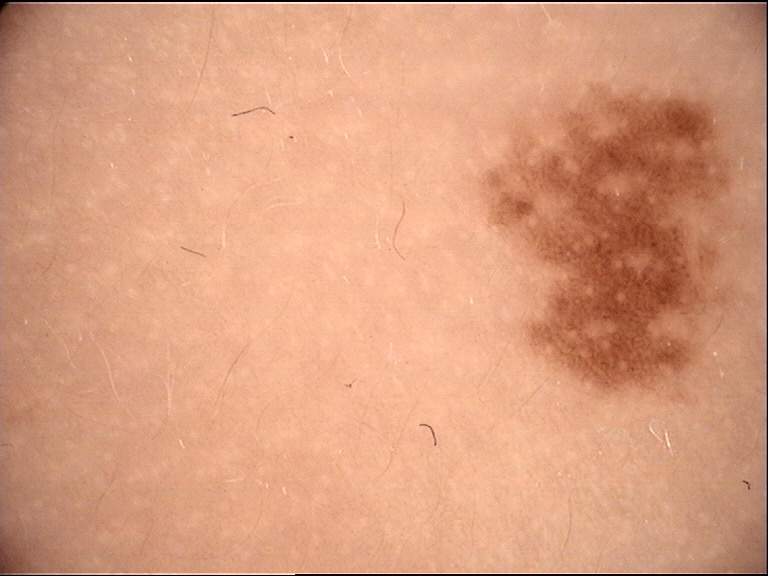Case:
- imaging — dermoscopy
- diagnostic label — congenital junctional nevus (expert consensus)